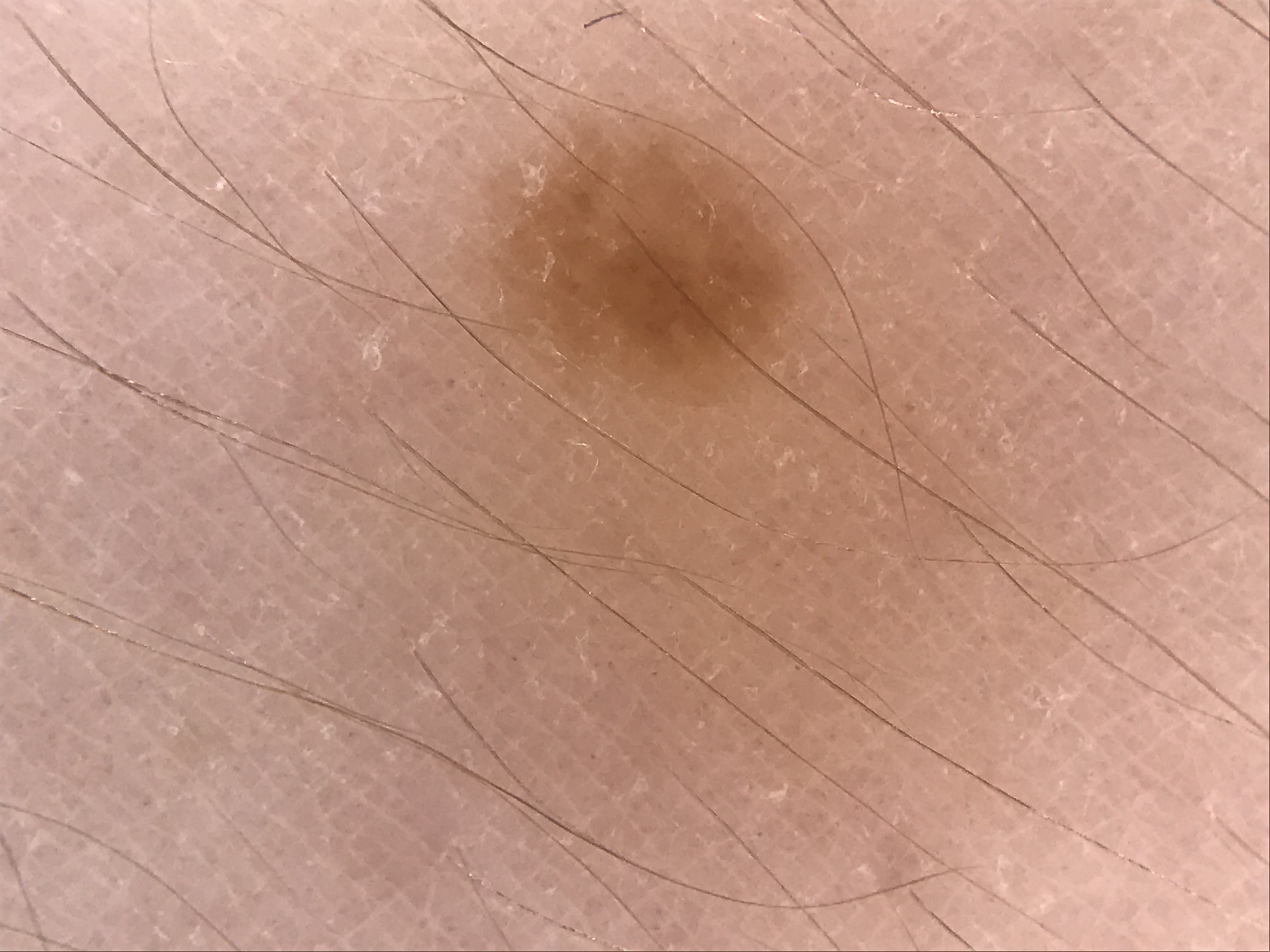The morphology is that of a banal lesion. Consistent with a junctional nevus.